The contributor notes the lesion is raised or bumpy, self-categorized by the patient as a rash, the patient reported no systemic symptoms, the affected area is the arm, the photograph was taken at a distance, the condition has been present for less than one week — 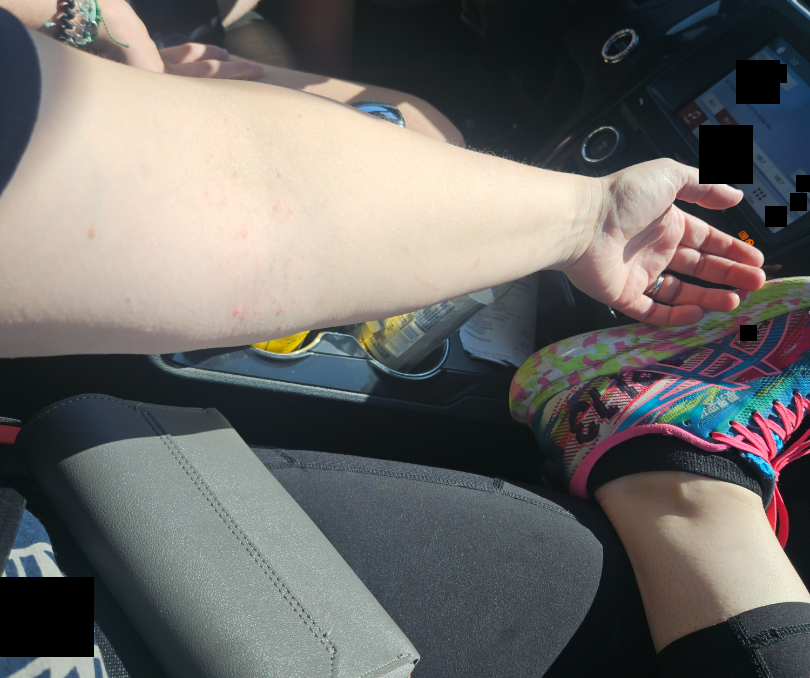On remote dermatologist review: most consistent with Eczema.